A dermatoscopic image of a skin lesion.
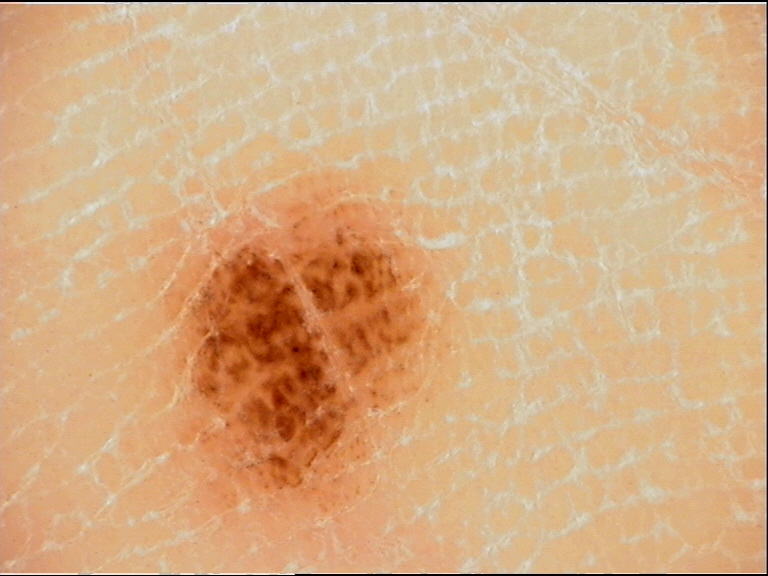{"diagnosis": {"name": "acral junctional nevus", "code": "ajb", "malignancy": "benign", "super_class": "melanocytic", "confirmation": "expert consensus"}}